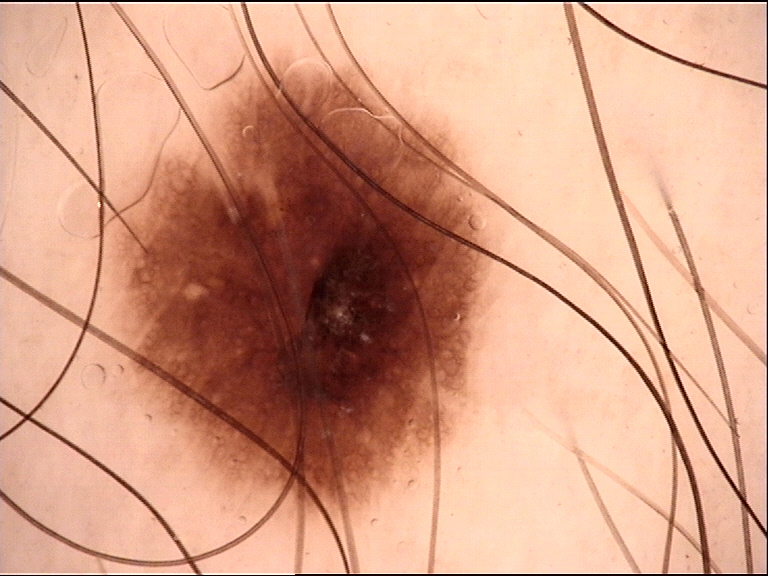assessment=dysplastic junctional nevus (expert consensus)